A male patient aged 38-42 · a contact-polarized dermoscopy image of a skin lesion — 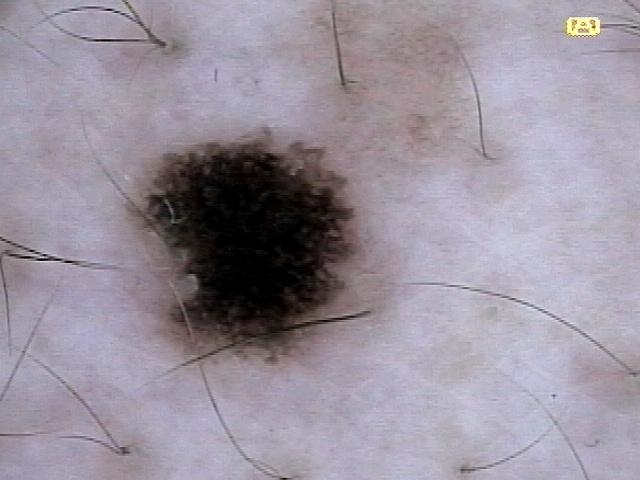diagnostic label: Nevus (biopsy-proven).